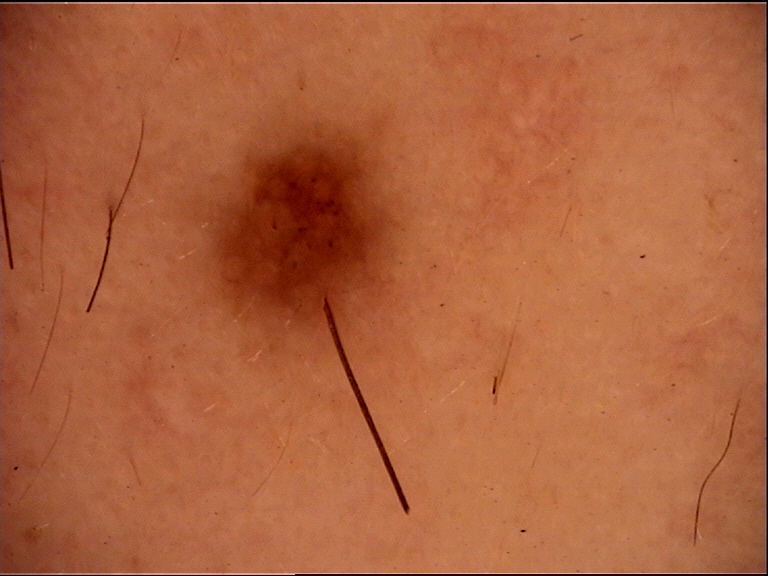lesion type = compound, banal | label = Miescher nevus (expert consensus).